A male patient aged 78. The patient describes having few moles overall. Dermoscopy of a skin lesion. The patient says their skin reddens with sun exposure. Collected as part of a research study, without a referral diagnosis.
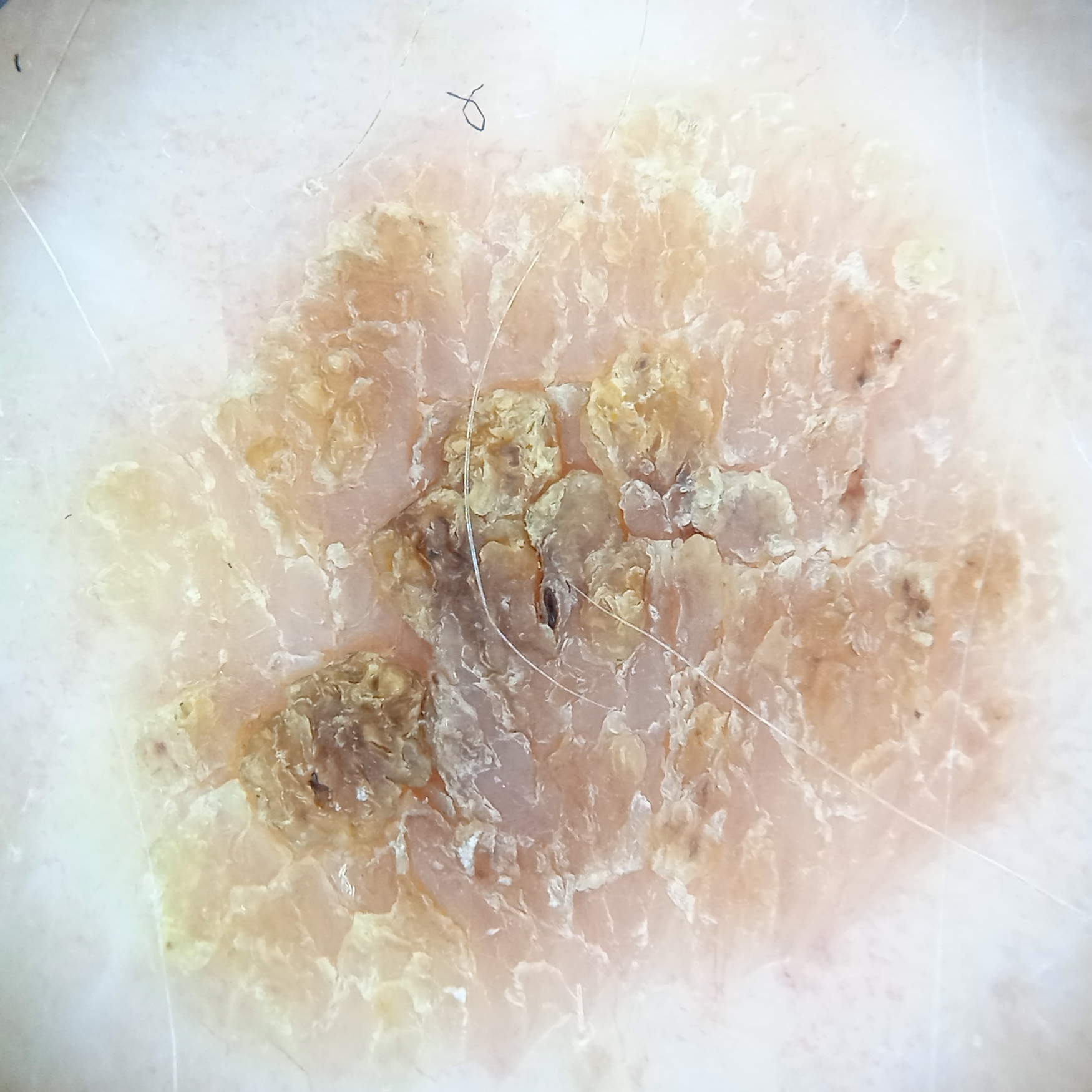Q: What was the diagnosis?
A: seborrheic keratosis (dermatologist consensus)